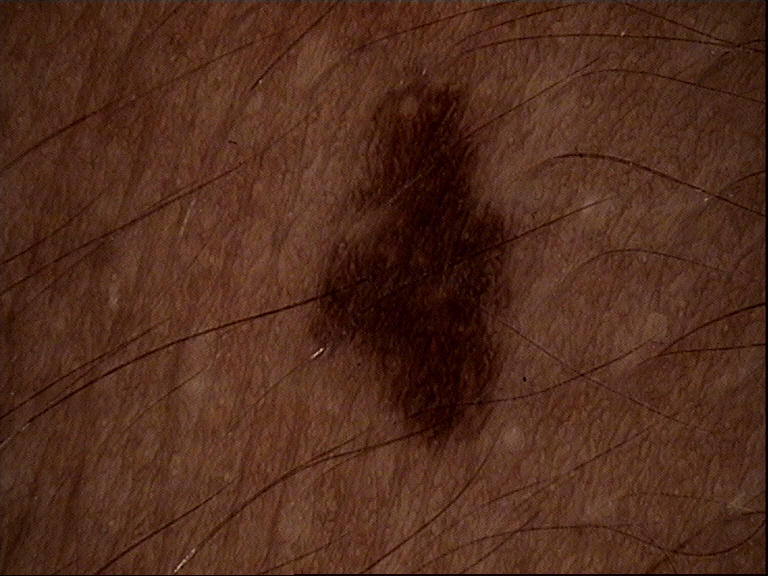The diagnostic label was a dysplastic junctional nevus.